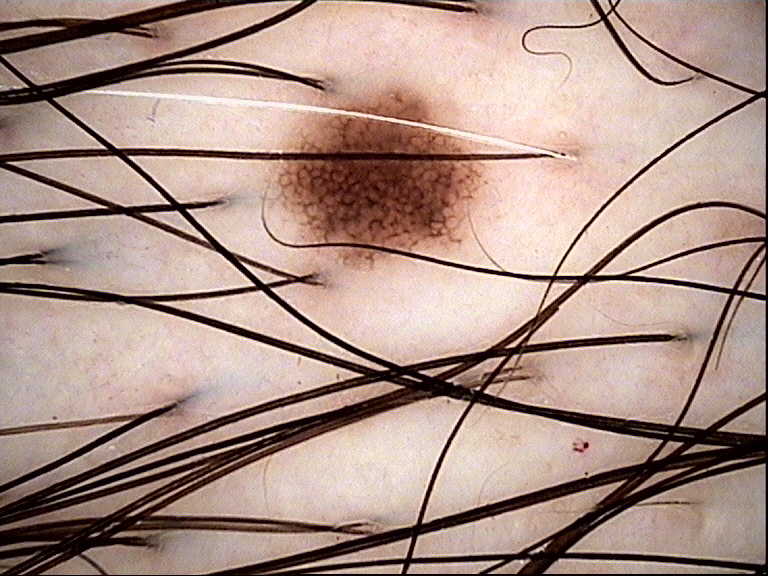Case:
* image type: dermatoscopy
* label: dysplastic junctional nevus (expert consensus)